A close-up photograph · the leg is involved · female patient, age 50–59.
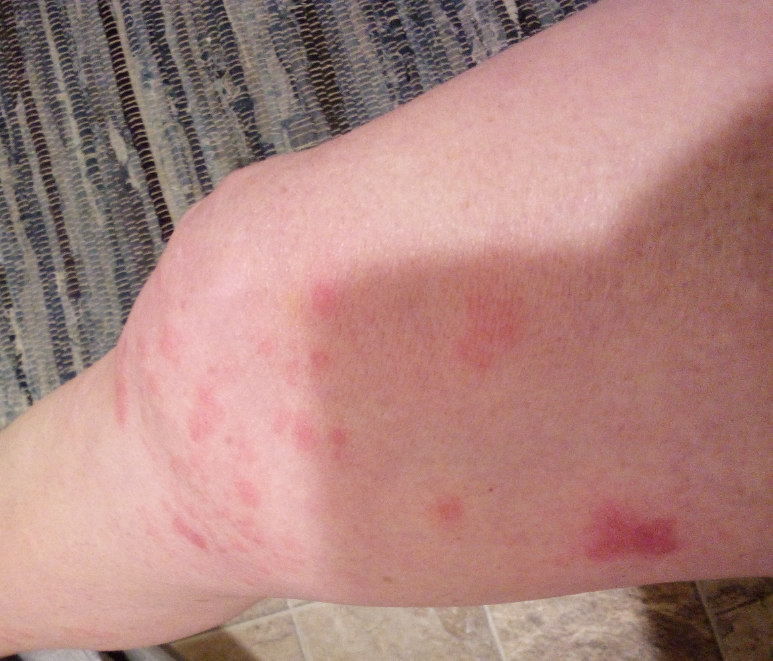Texture is reported as raised or bumpy. Skin tone: Fitzpatrick I; lay graders estimated MST 2. The patient described the issue as a rash. The patient indicates burning, darkening, bothersome appearance and itching. The patient indicates the condition has been present for less than one week. Associated systemic symptoms include joint pain. The reviewing dermatologist's impression was: Urticaria, Insect Bite and Allergic Contact Dermatitis were considered with similar weight.